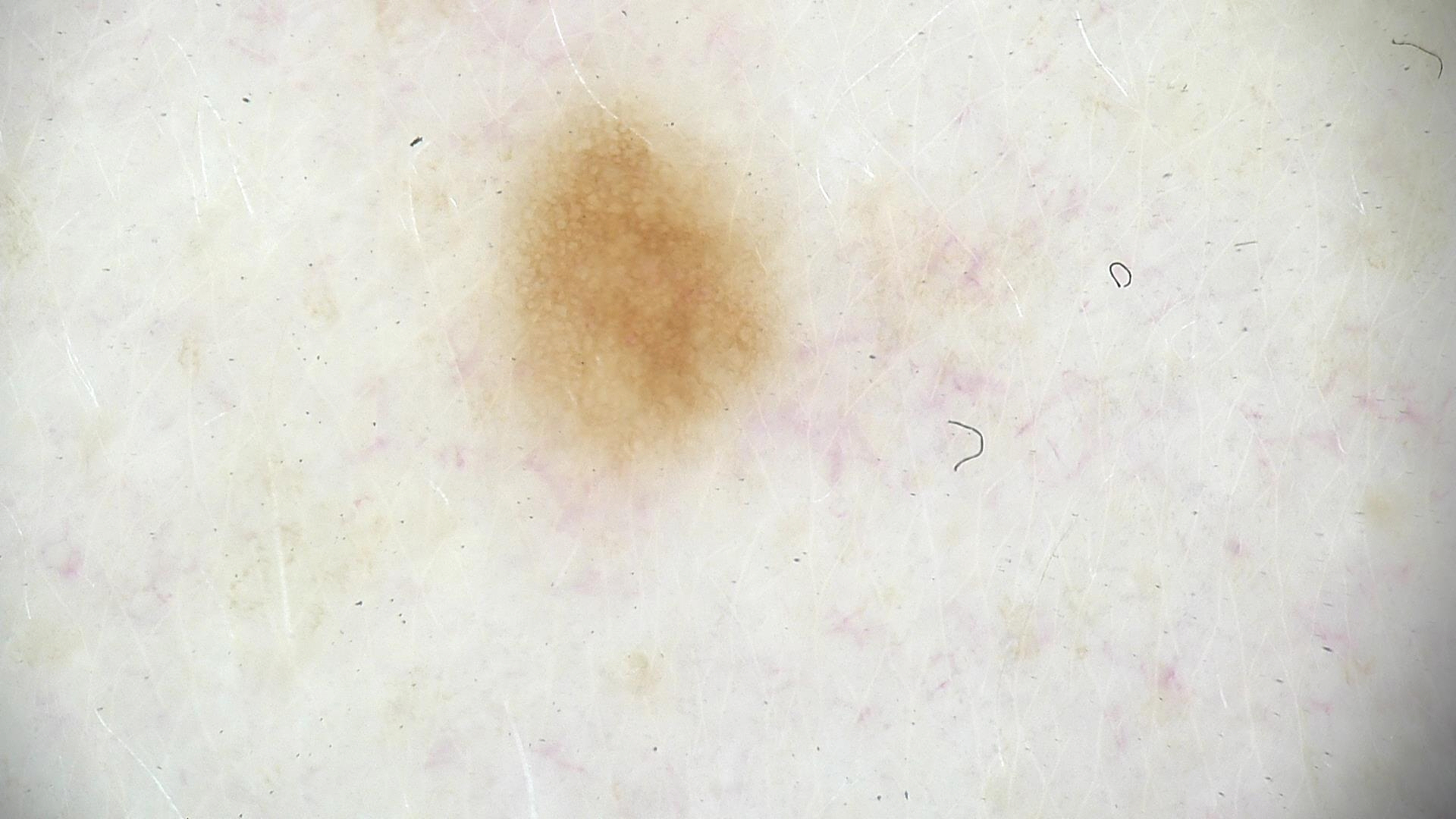Findings:
A skin lesion imaged with a dermatoscope.
Conclusion:
Diagnosed as a benign lesion — a dysplastic junctional nevus.